The patient described the issue as a rash. The patient reports the lesion is flat. The lesion involves the leg. Present for about one day. Female subject, age 30–39. No relevant lesion symptoms reported. An image taken at a distance:
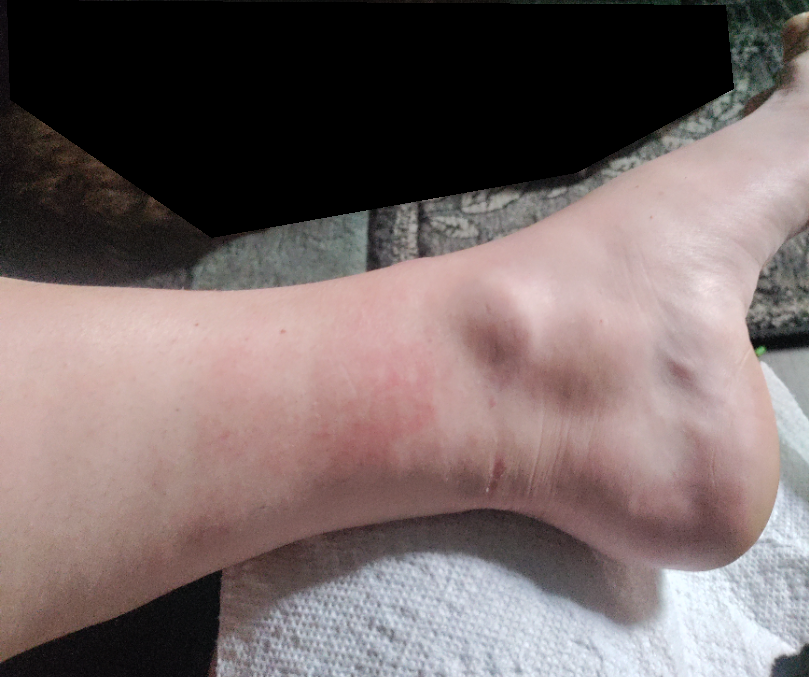Impression: The differential, in no particular order, includes Stasis Dermatitis; Acute dermatitis, NOS; and Allergic Contact Dermatitis.